Texture is reported as raised or bumpy · the lesion is associated with itching · the leg, back of the hand, palm and arm are involved · the patient described the issue as a rash · the patient reported no systemic symptoms · the photograph is a close-up of the affected area · the condition has been present for less than one week.
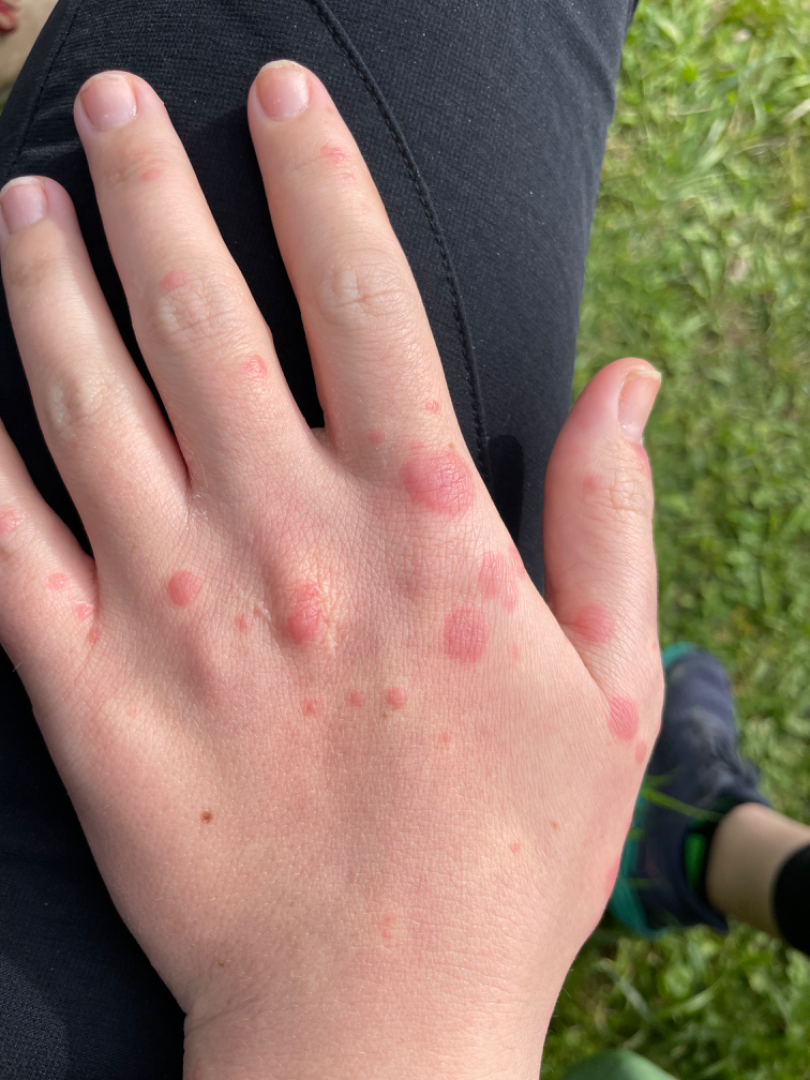- assessment: ungradable on photographic review